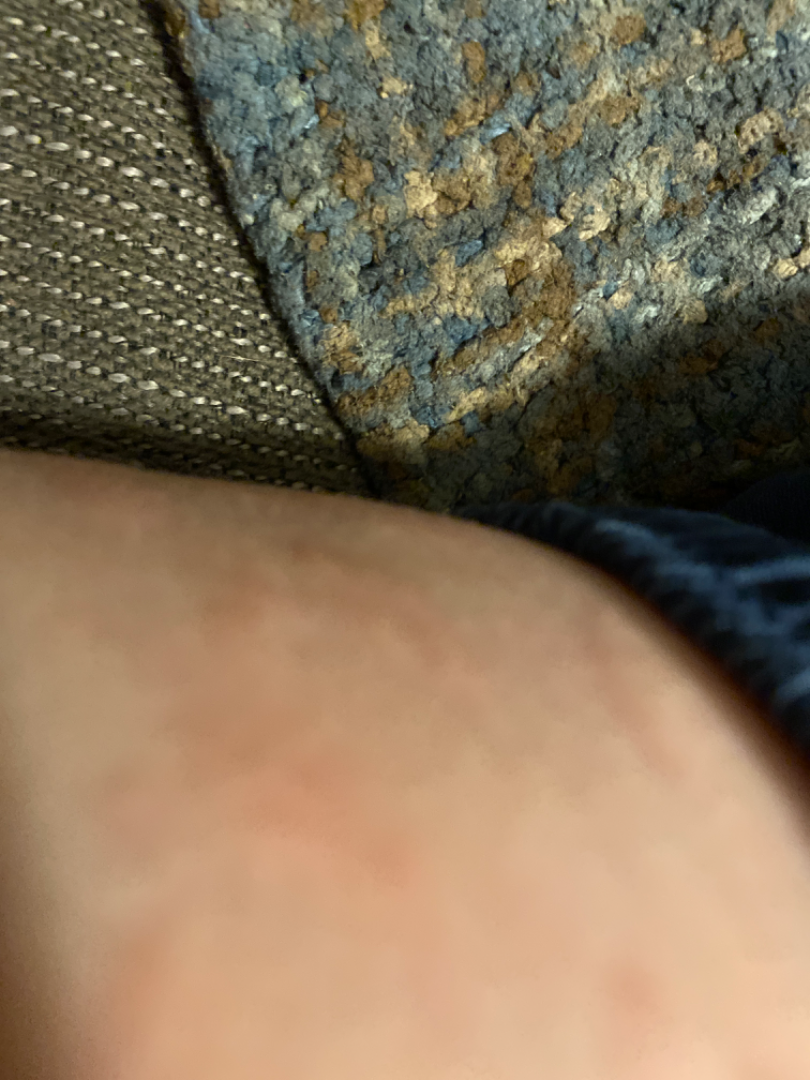  shot_type: at an angle
  texture: raised or bumpy
  symptoms: itching
  differential:
    leading:
      - Urticaria